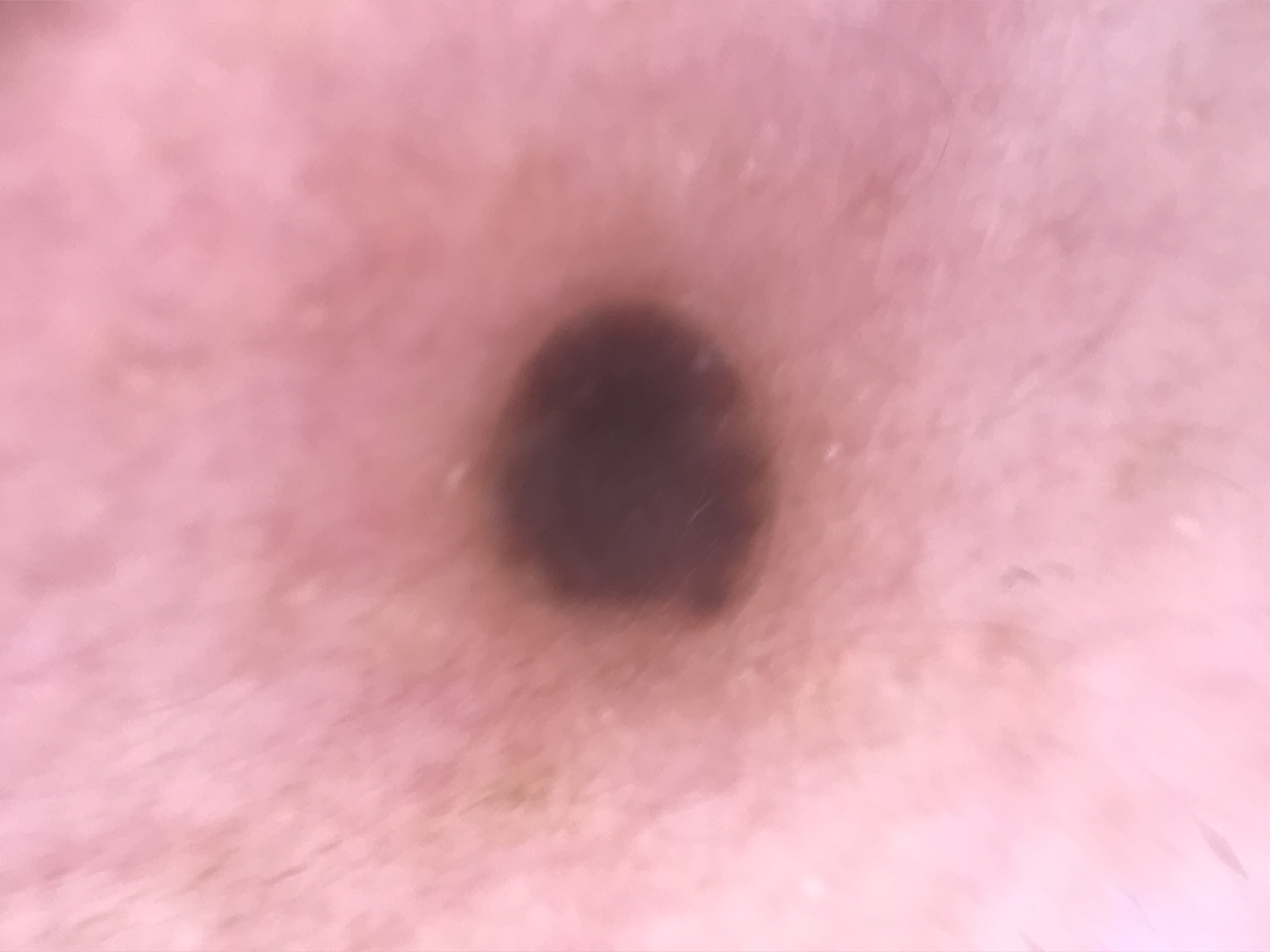classification=banal | label=compound nevus (expert consensus).